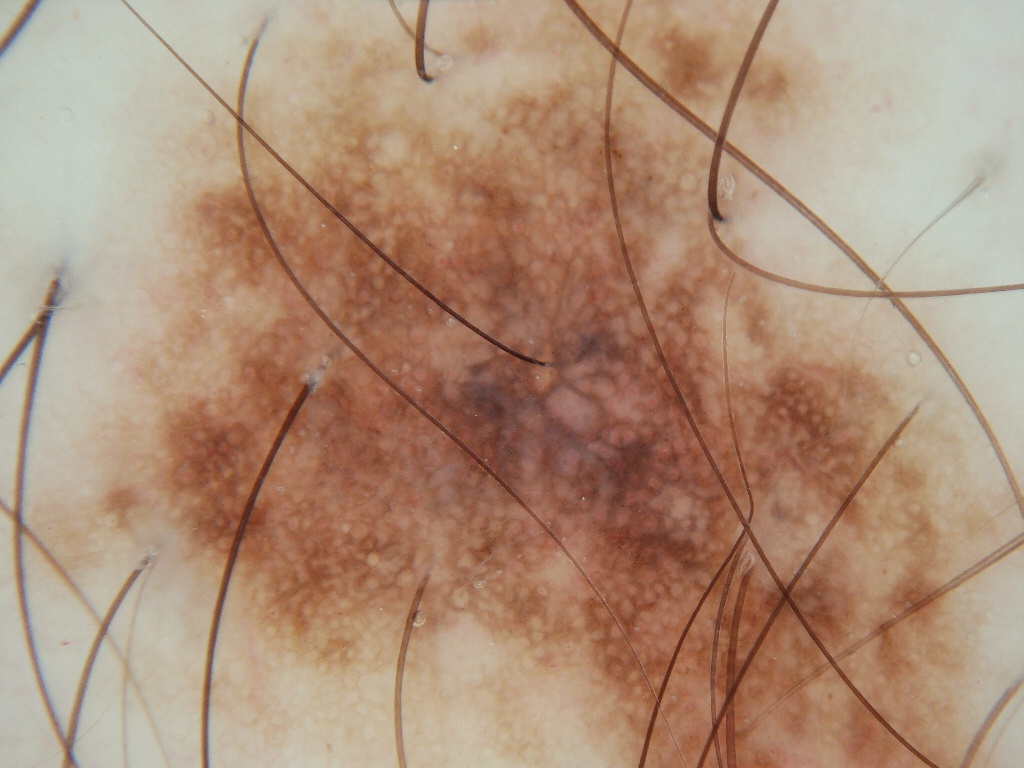The subject is a male roughly 30 years of age.
A dermoscopic image of a skin lesion.
Dermoscopic review identifies pigment network; no streaks, negative network, globules, or milia-like cysts.
The lesion extends across almost the whole field of view.
The clinical diagnosis was a melanocytic nevus.